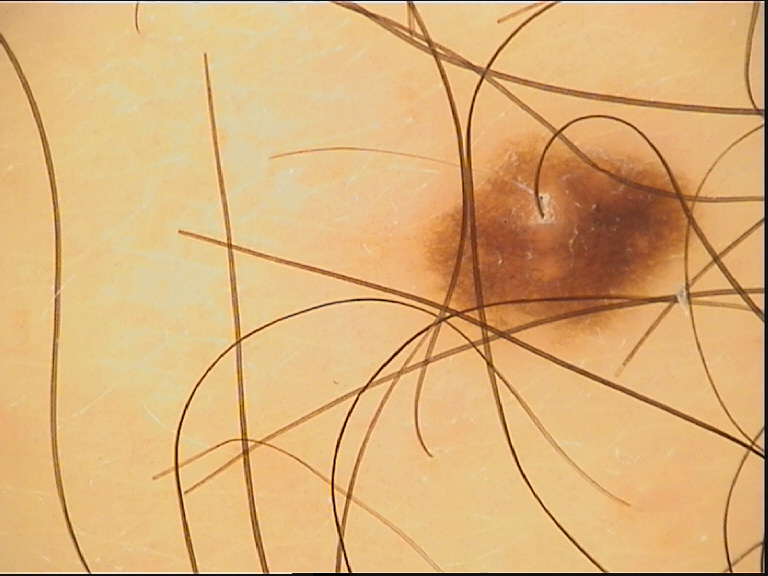| field | value |
|---|---|
| image | dermoscopy |
| diagnosis | junctional nevus (expert consensus) |